This is a close-up image; the patient considered this a rash; the lesion is associated with itching and bothersome appearance; the subject is 70–79, female; the lesion involves the head or neck and back of the hand; the condition has been present for less than one week:
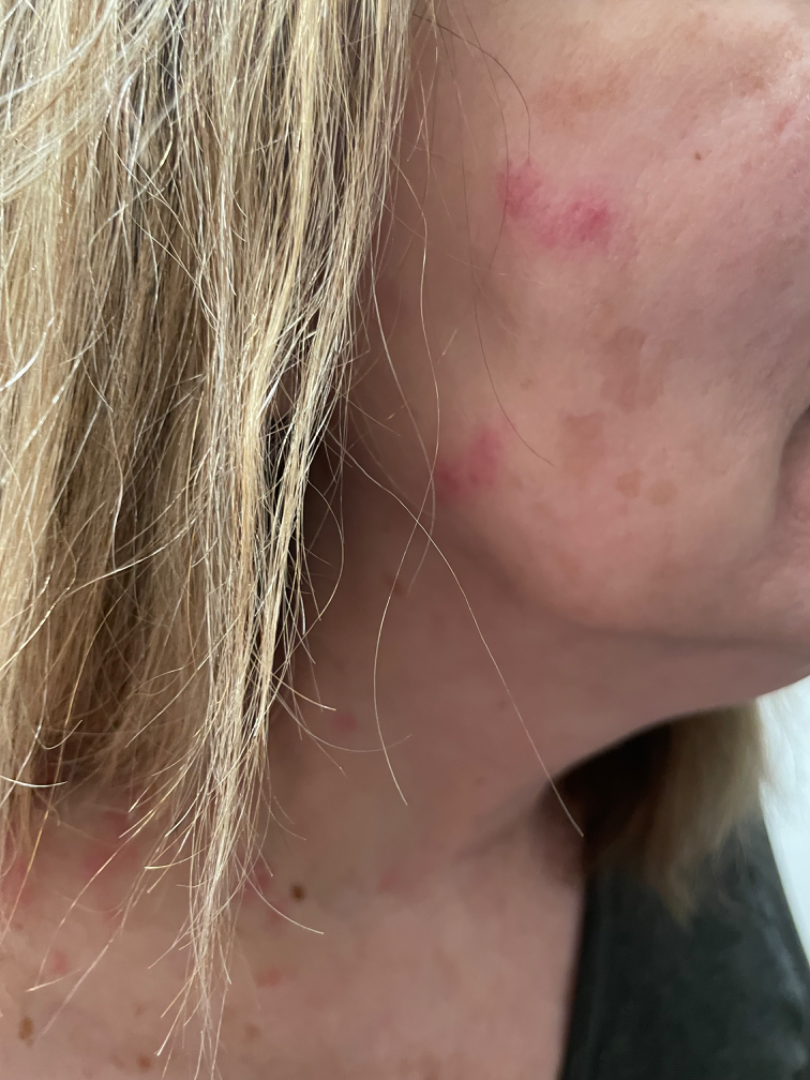The skin condition could not be confidently assessed from this image.